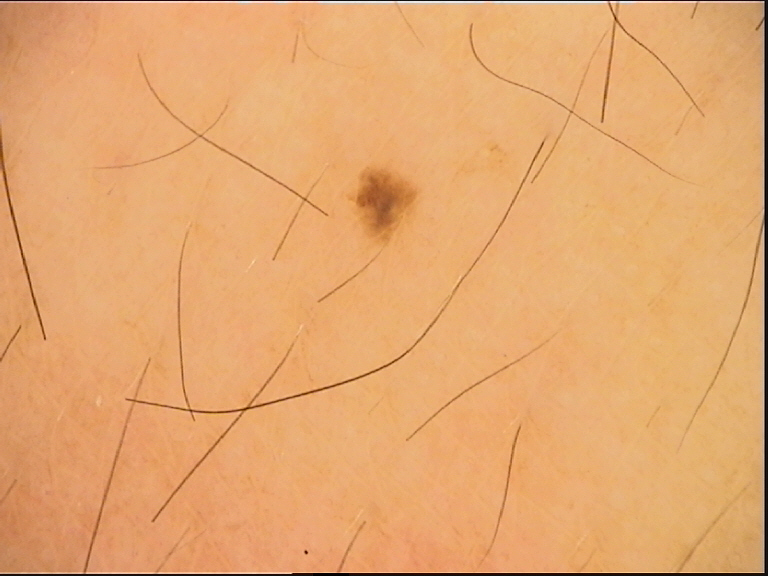A dermoscopy image of a single skin lesion. Diagnosed as a junctional nevus.